The contributor is a female aged 50–59; the lesion involves the leg; a close-up photograph — 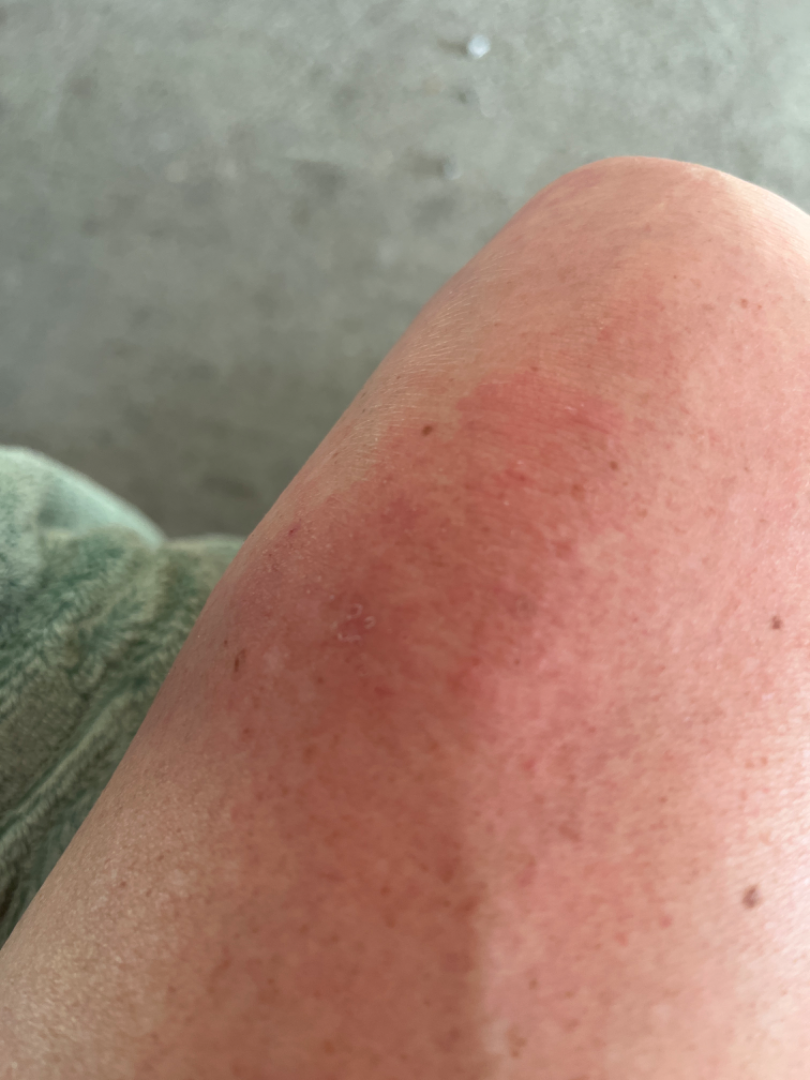Q: Reported symptoms?
A: itching
Q: When did this start?
A: one to three months
Q: How does the lesion feel?
A: raised or bumpy
Q: What is the patient's skin tone?
A: Fitzpatrick skin type II; lay reviewers estimated Monk skin tone scale 2–3
Q: Constitutional symptoms?
A: none reported
Q: Patient's own categorization?
A: a rash
Q: What is the differential diagnosis?
A: Eczema (weight 0.40); Allergic Contact Dermatitis (weight 0.23); Abrasion, scrape, or scab (weight 0.23); Psoriasis (weight 0.15)